A moderate number of moles by the patient's own estimate. A female patient aged 59.
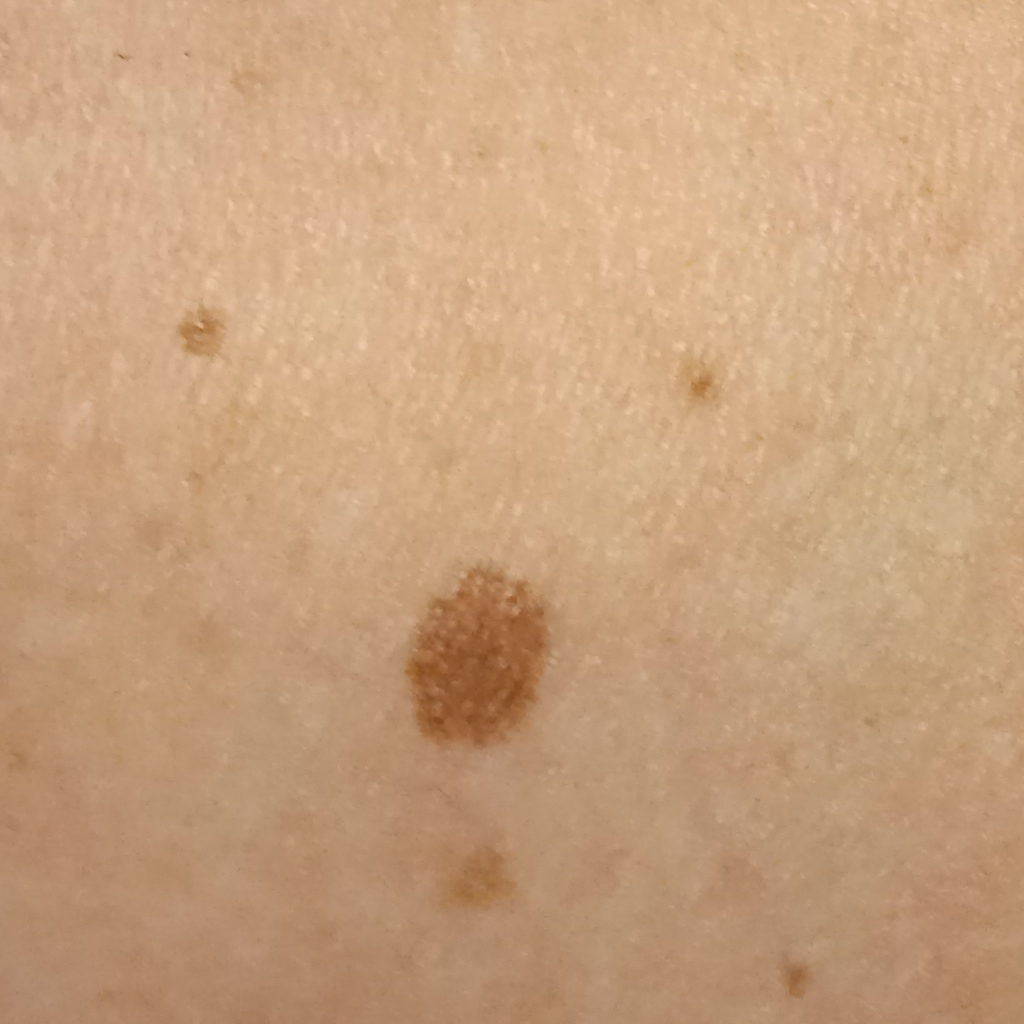| feature | finding |
|---|---|
| diagnosis | atypical (dysplastic) nevus — biopsy-proven |